A skin lesion imaged with a dermatoscope.
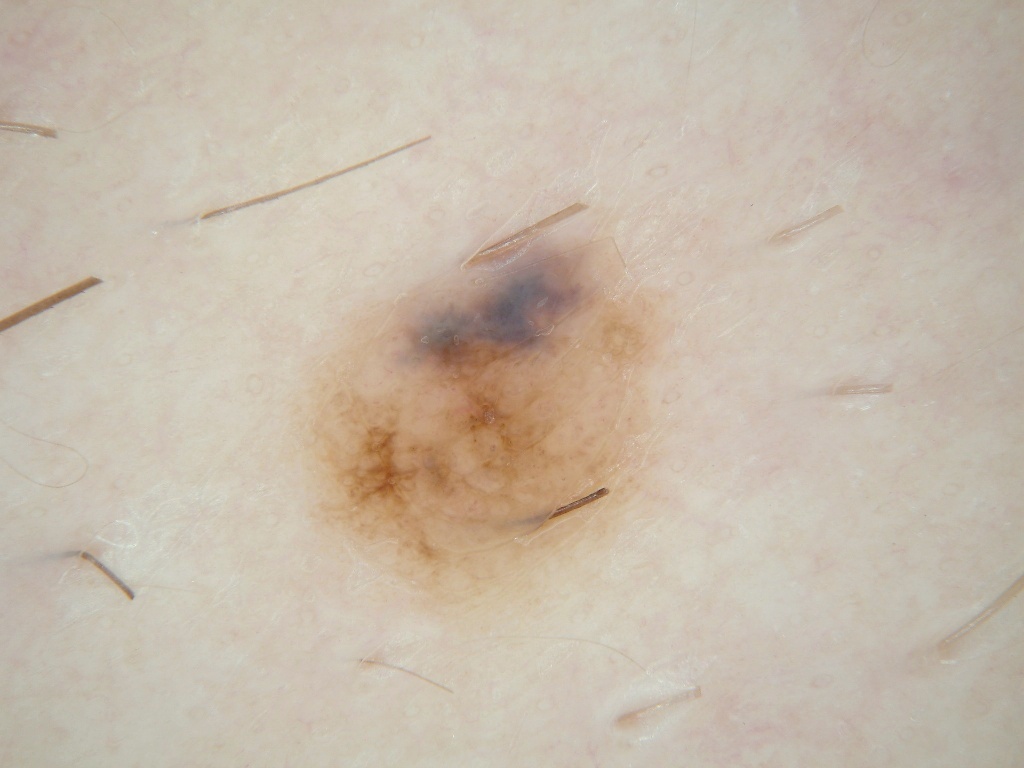The lesion spans <bbox>285, 195, 671, 622</bbox>. Dermoscopic review identifies no streaks, milia-like cysts, pigment network, negative network, or globules. The diagnostic assessment was a melanocytic nevus, a benign skin lesion.